An image taken at a distance — 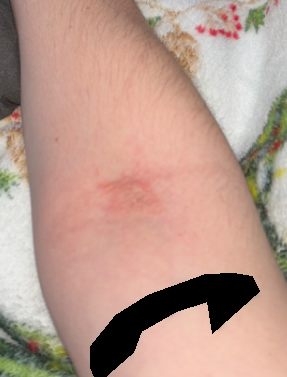differential:
  leading:
    - Eczema